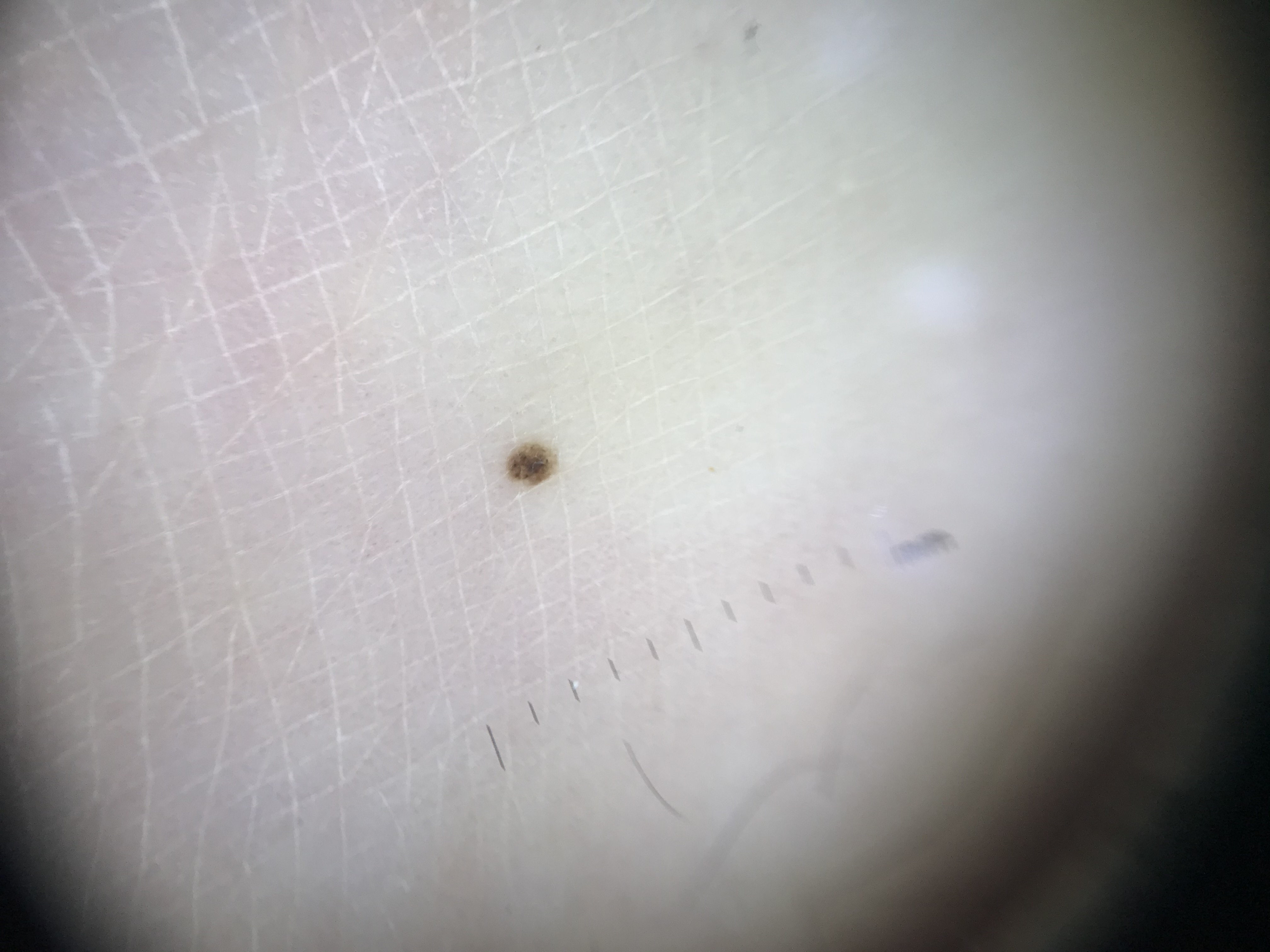Summary: A dermoscopic photograph of a skin lesion. Impression: Consistent with an acral junctional nevus.